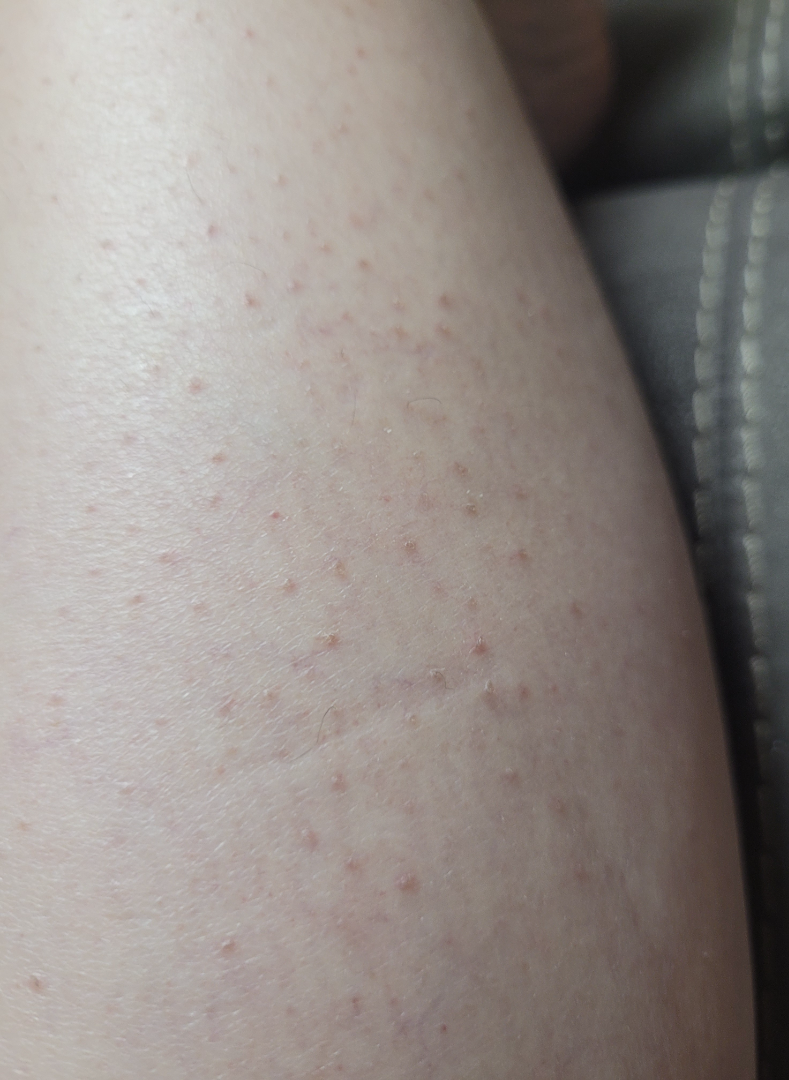– photo taken · close-up
– lesion symptoms · bothersome appearance
– anatomic site · leg
– impression · Keratosis pilaris (0.67); Folliculitis (0.33)